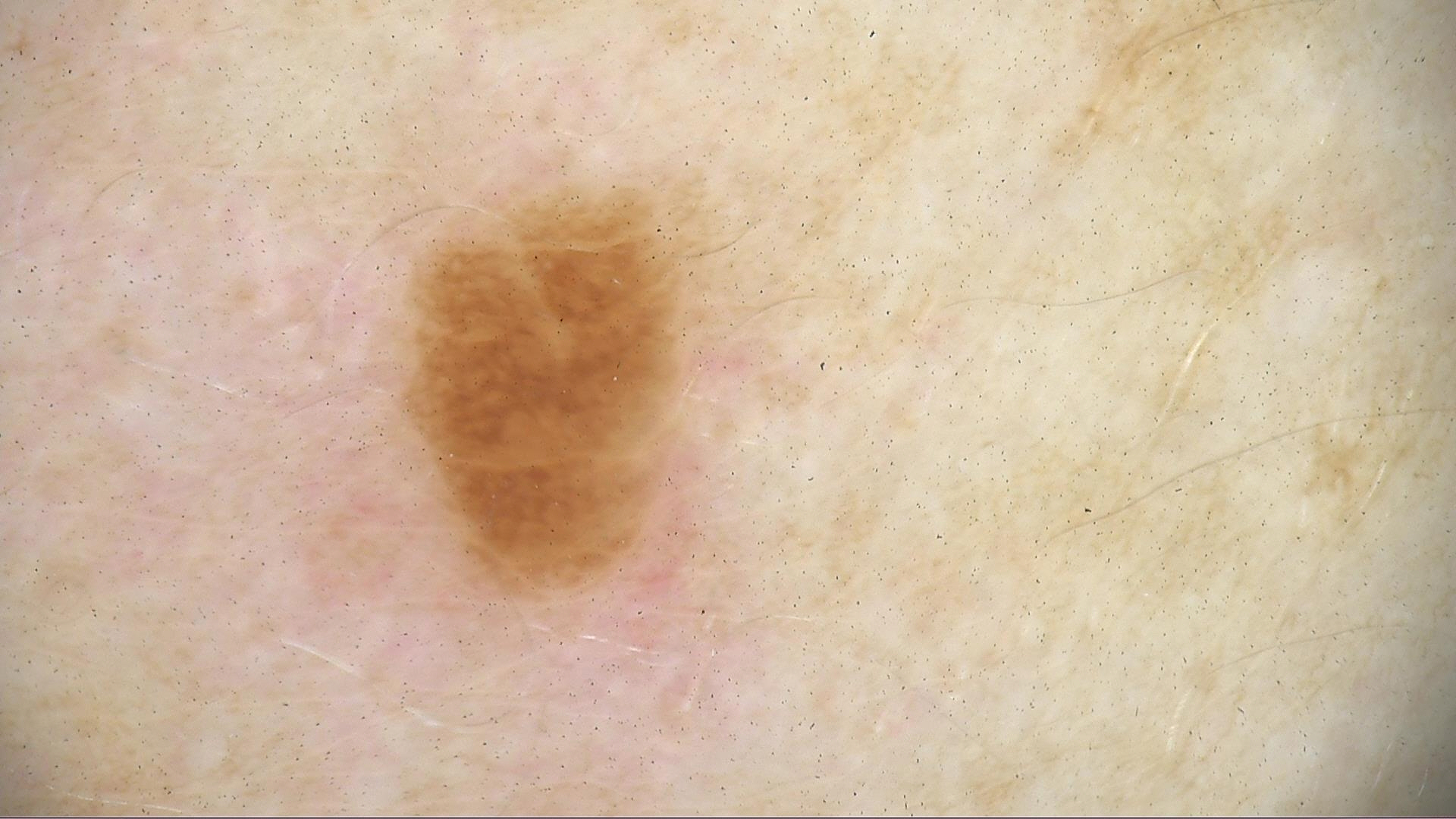Dermoscopy of a skin lesion. The morphology is that of a keratinocytic lesion. The diagnosis was a seborrheic keratosis.